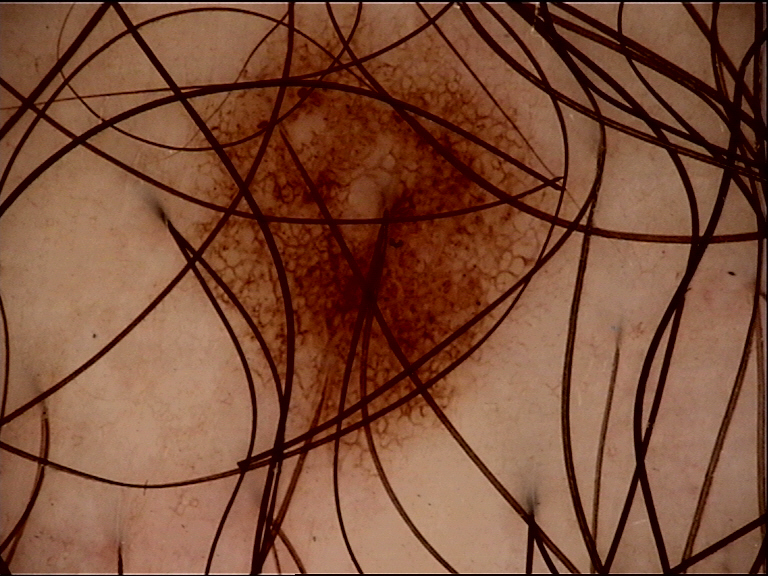label: junctional nevus (expert consensus).